A dermoscopic image of a skin lesion.
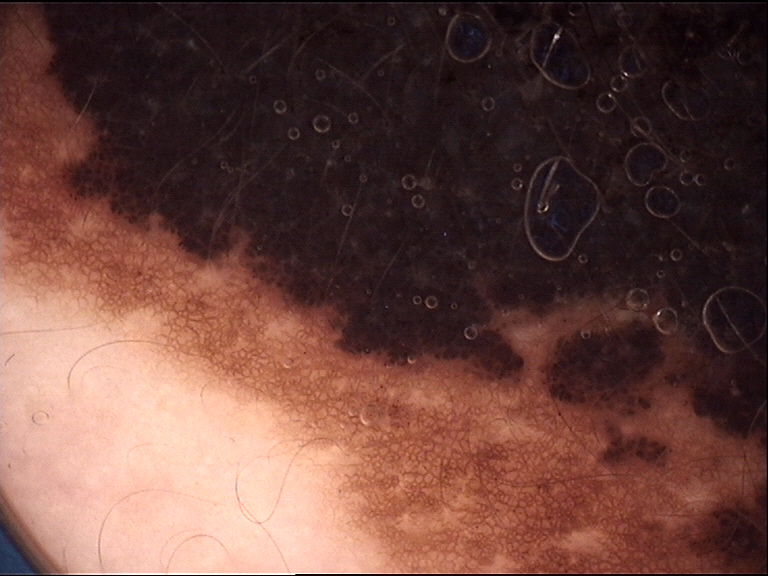category: banal; diagnostic label: congenital compound nevus (expert consensus).